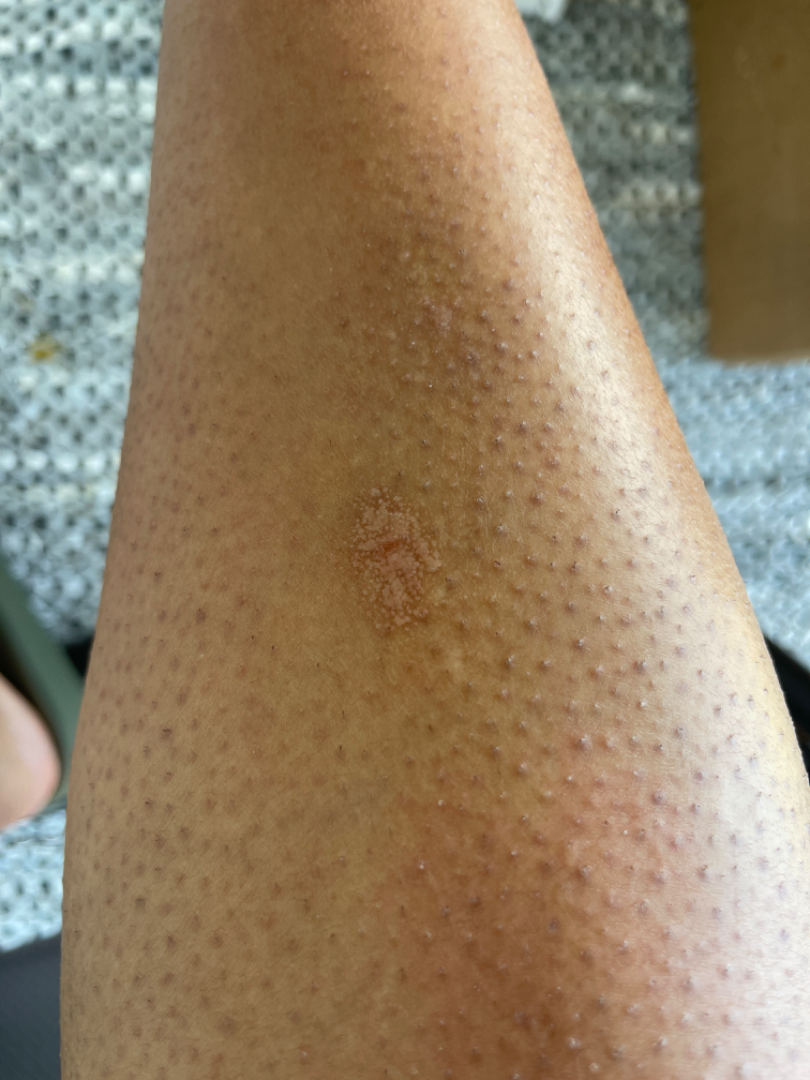Female patient, age 30–39. Self-categorized by the patient as a rash. Present for more than one year. A close-up photograph. FST IV. Symptoms reported: bothersome appearance and itching. The contributor reports the lesion is rough or flaky and raised or bumpy. Located on the leg. On dermatologist assessment of the image, most consistent with Verruca vulgaris.